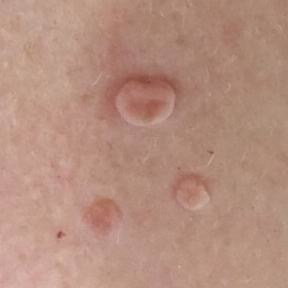A female patient aged 55.
A smartphone photograph of a skin lesion.
By history, pesticide exposure, prior skin cancer (patient or family), no prior malignancy (patient or family), and no alcohol use.
The lesion is on the back.
The lesion is roughly 5 by 5 mm.
Per patient report, the lesion is elevated, but does not hurt and does not itch.
Consistent with a nevus.